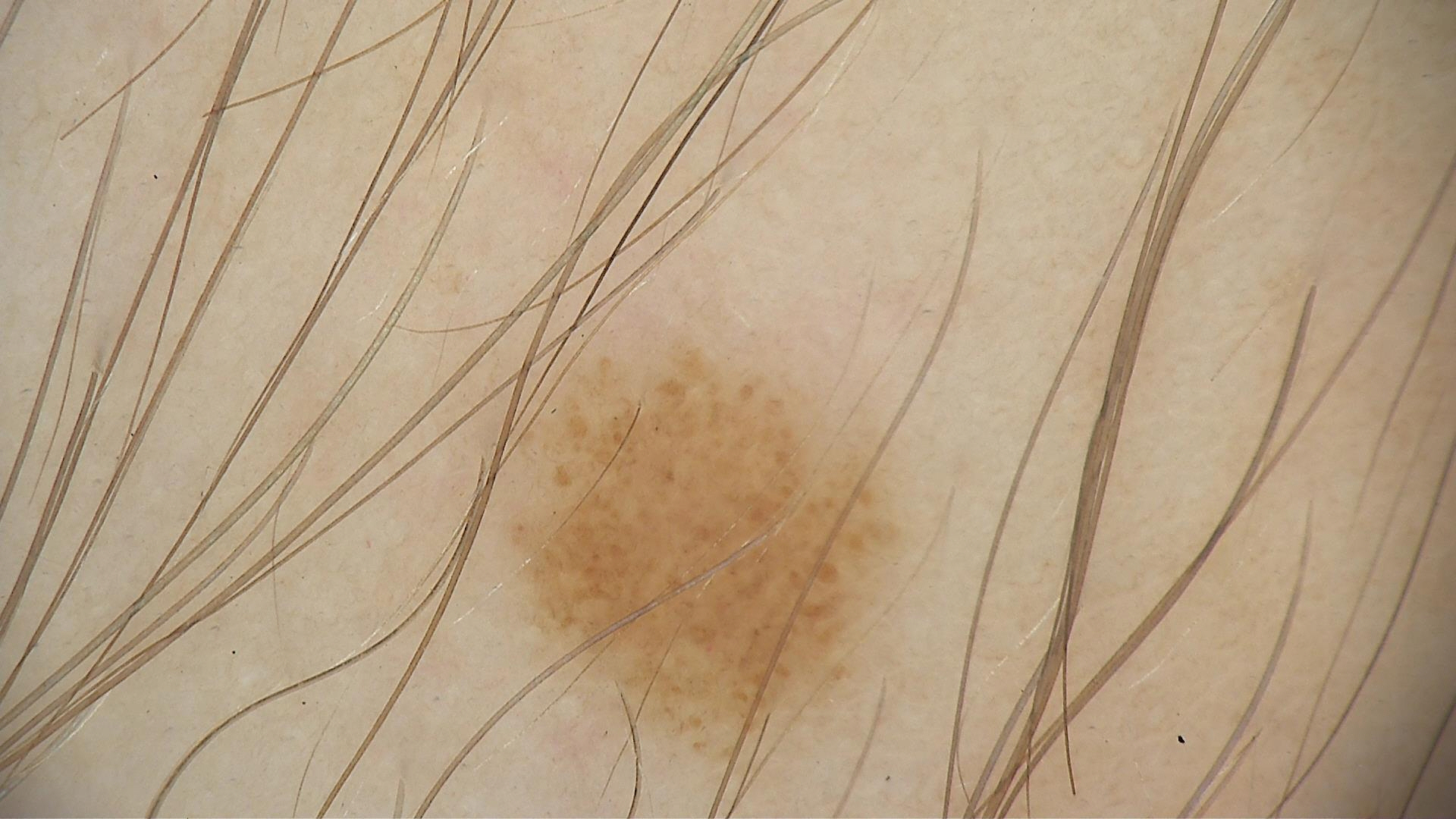A skin lesion imaged with a dermatoscope. Diagnosed as a benign lesion — a dysplastic junctional nevus.